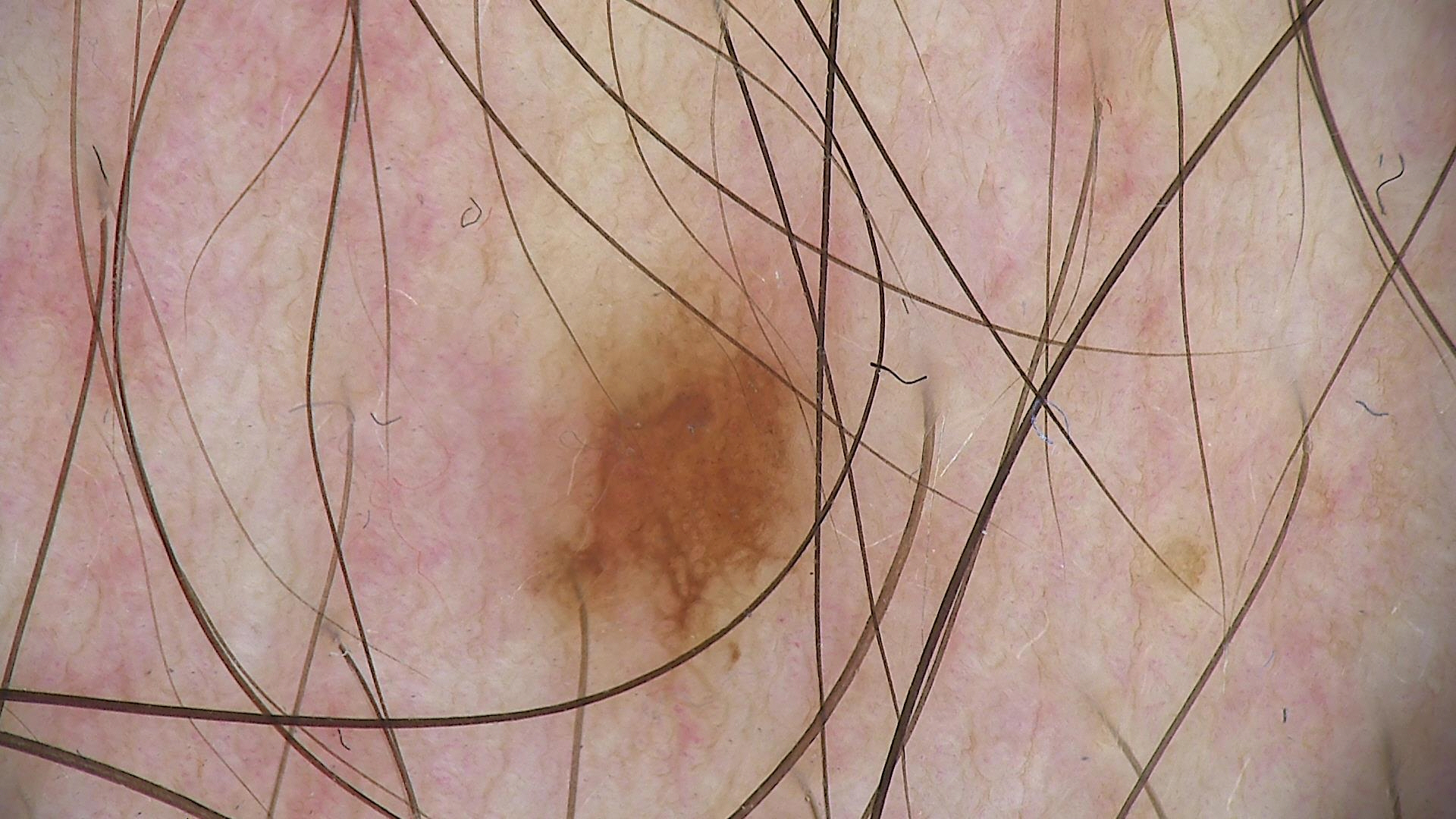Q: What kind of image is this?
A: dermatoscopy
Q: What is the diagnosis?
A: dysplastic junctional nevus (expert consensus)